A patient age 75. A clinical photograph of a skin lesion: 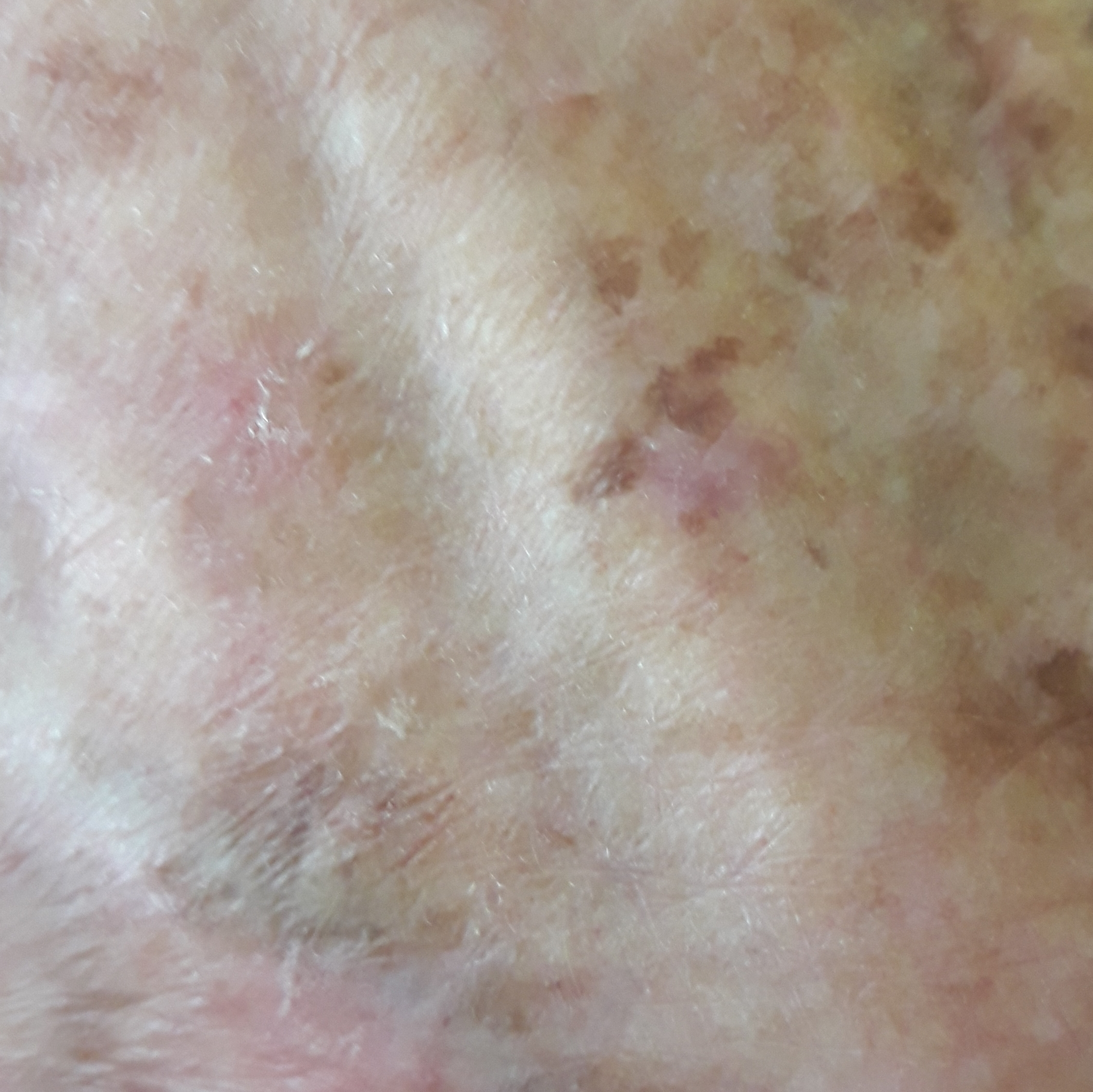Summary: Located on a hand. The patient describes that the lesion itches, but is not elevated and does not hurt. Impression: Diagnosed by dermatologist consensus as an actinic keratosis.